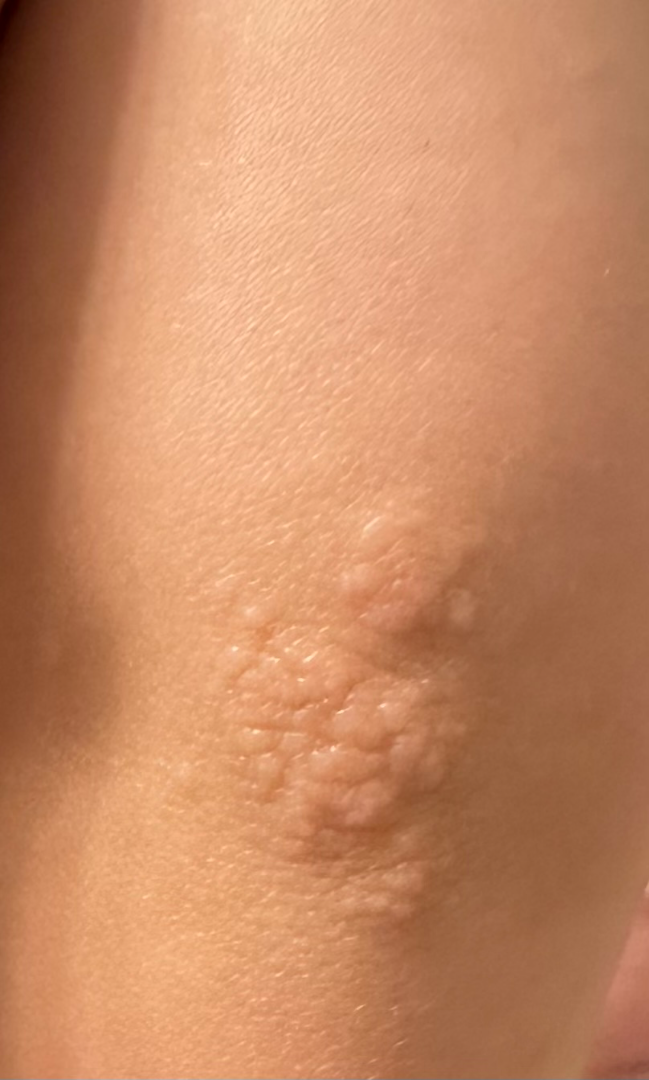{"patient": "male", "shot_type": "close-up", "body_site": "arm", "differential": {"tied_lead": ["Epidermal nevus", "Verruca vulgaris", "Psoriasis"]}}